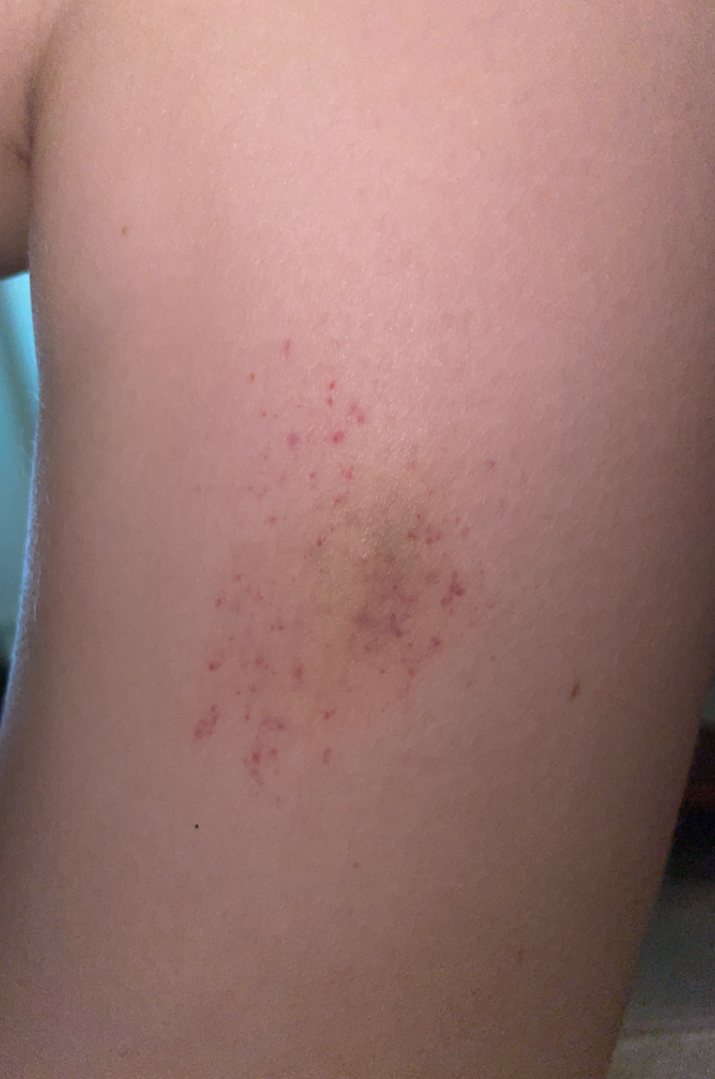| key | value |
|---|---|
| symptoms | none reported |
| described texture | raised or bumpy |
| patient's own categorization | a rash |
| site | leg |
| shot type | close-up |
| duration | about one day |